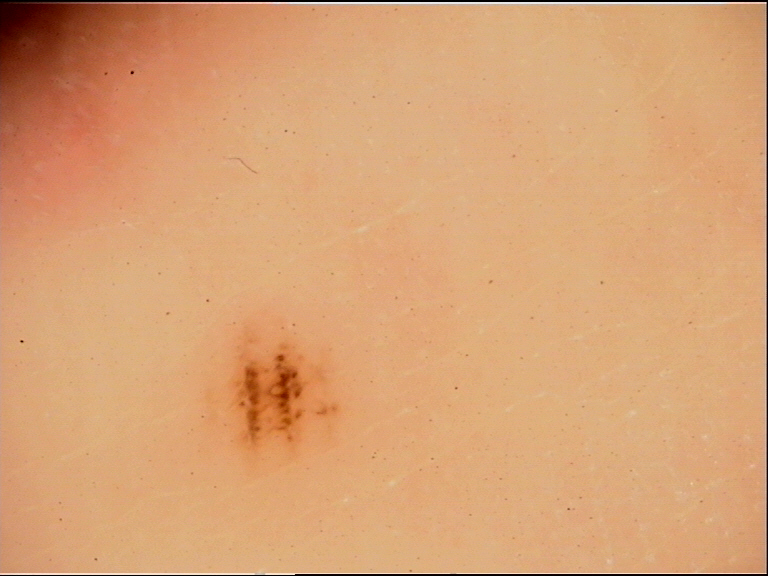{"image": "dermatoscopy", "lesion_type": {"main_class": "banal", "pattern": "junctional"}, "diagnosis": {"name": "acral junctional nevus", "code": "ajb", "malignancy": "benign", "super_class": "melanocytic", "confirmation": "expert consensus"}}